The patient considered this a rash. No relevant systemic symptoms. Present for about one day. Reported lesion symptoms include itching and enlargement. The lesion involves the arm. This image was taken at an angle. FST IV; lay graders estimated Monk Skin Tone 2 or 5 (two reviewer pools disagreed). The lesion is described as raised or bumpy: 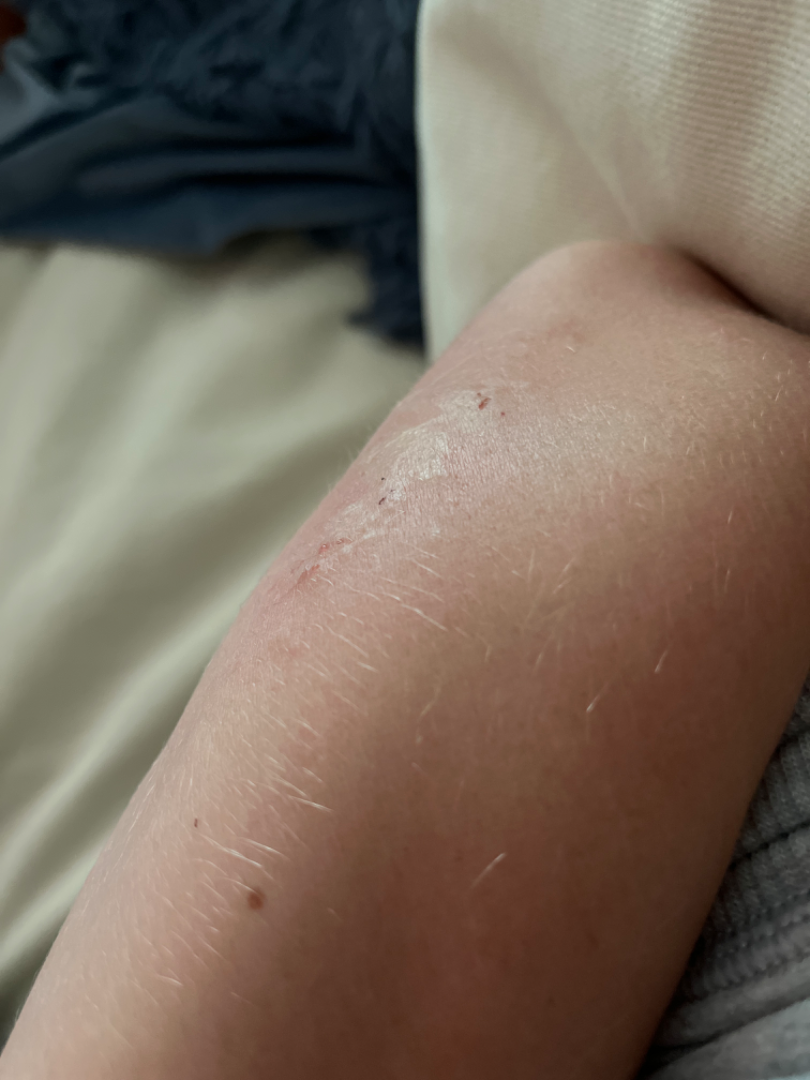Most consistent with Urticaria.